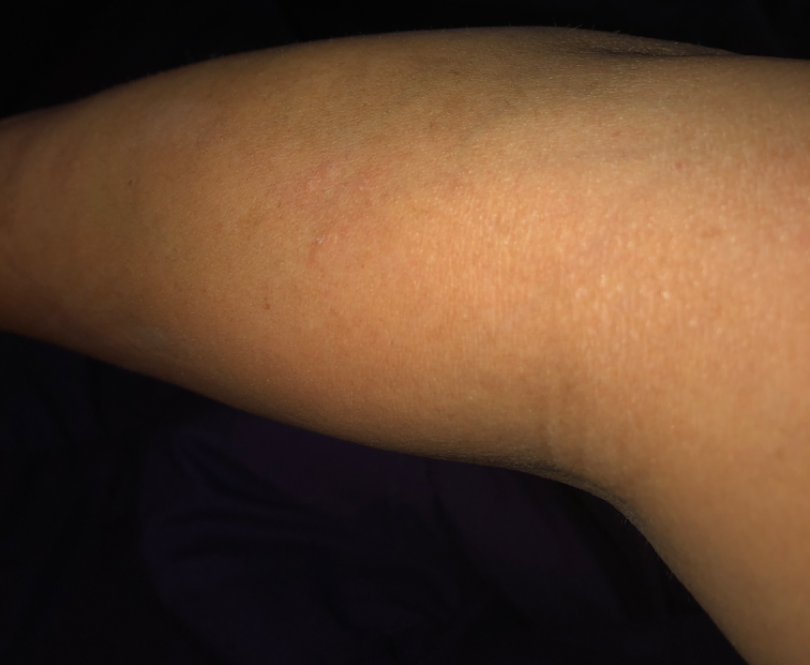Patient information:
The photo was captured at a distance. The arm is involved. The patient is a female aged 40–49.
Review:
Three dermatologists each reviewed the case: the leading consideration is Eczema; also raised was Lichenoid myxedema; also on the differential is Discrete papular lichen myxedematosus.